Imaged for a research study, with no referral diagnosis recorded · a clinical photograph of a skin lesion · a male patient 66 years old.
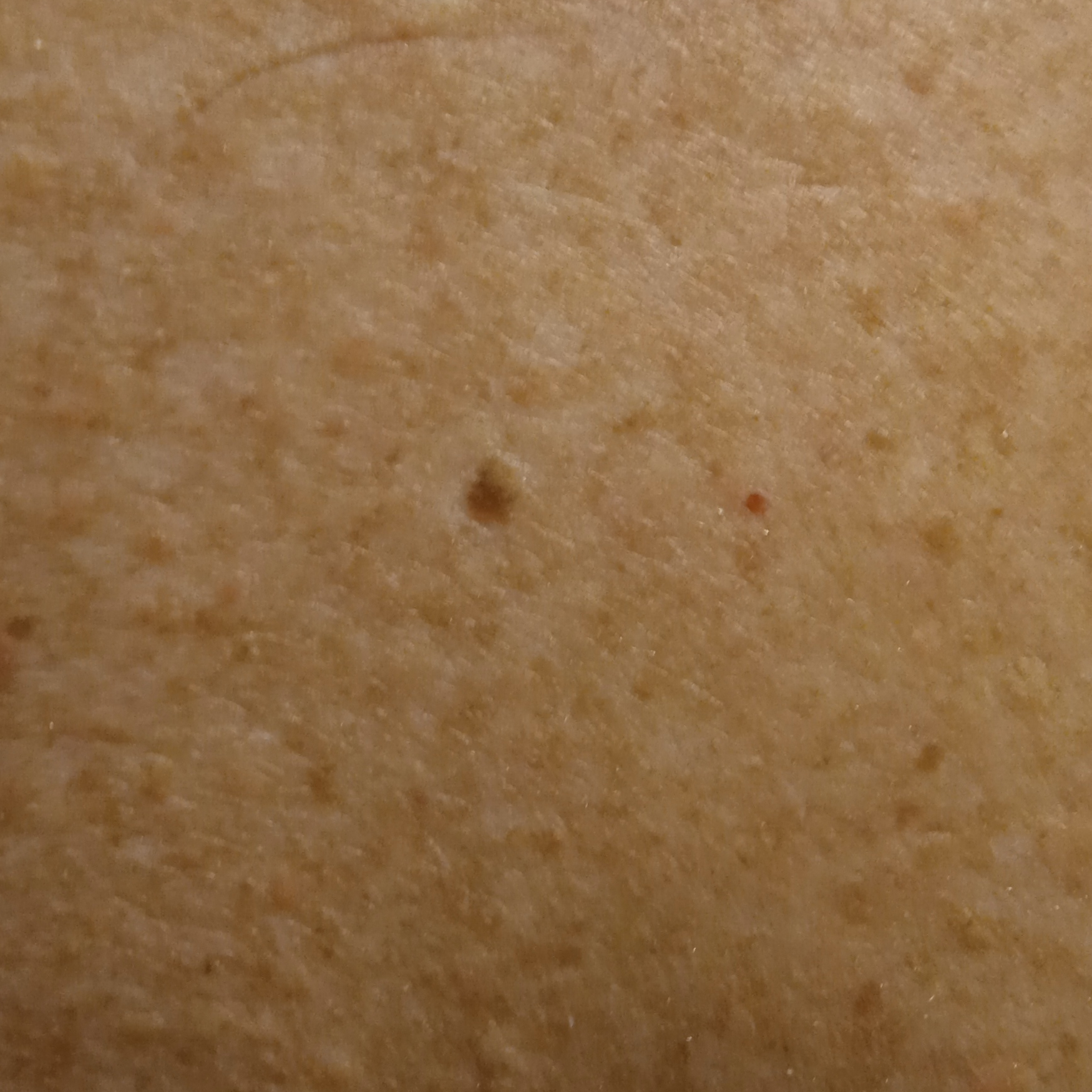The lesion is on the back. Measuring roughly 4.5 mm. The dermatologists' assessment was a seborrheic keratosis.